A dermatoscopic image of a skin lesion:
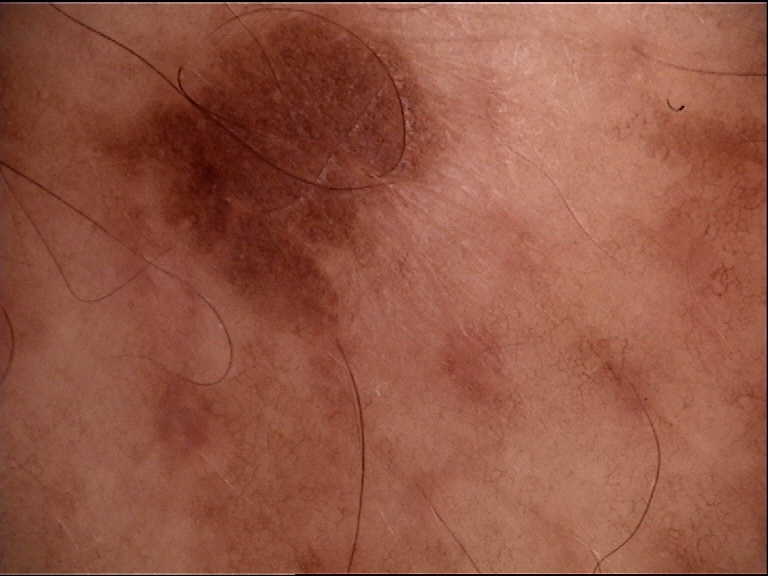The diagnosis was a benign lesion — a dysplastic junctional nevus.